A dermoscopic image of a skin lesion:
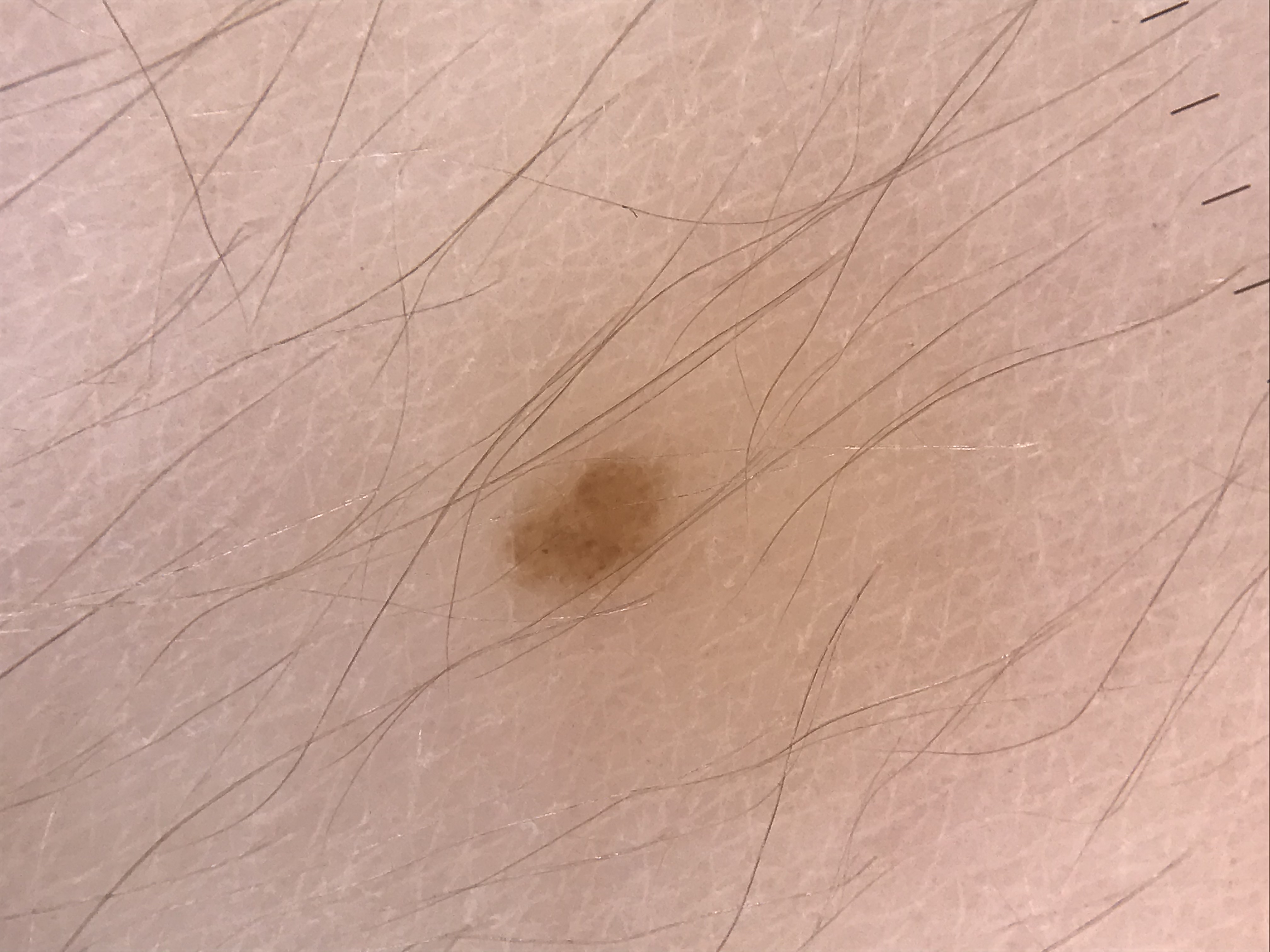Findings: The morphology is that of a banal lesion. Impression: The diagnostic label was a junctional nevus.